A clinical close-up photograph of a skin lesion. A male subject age 70:
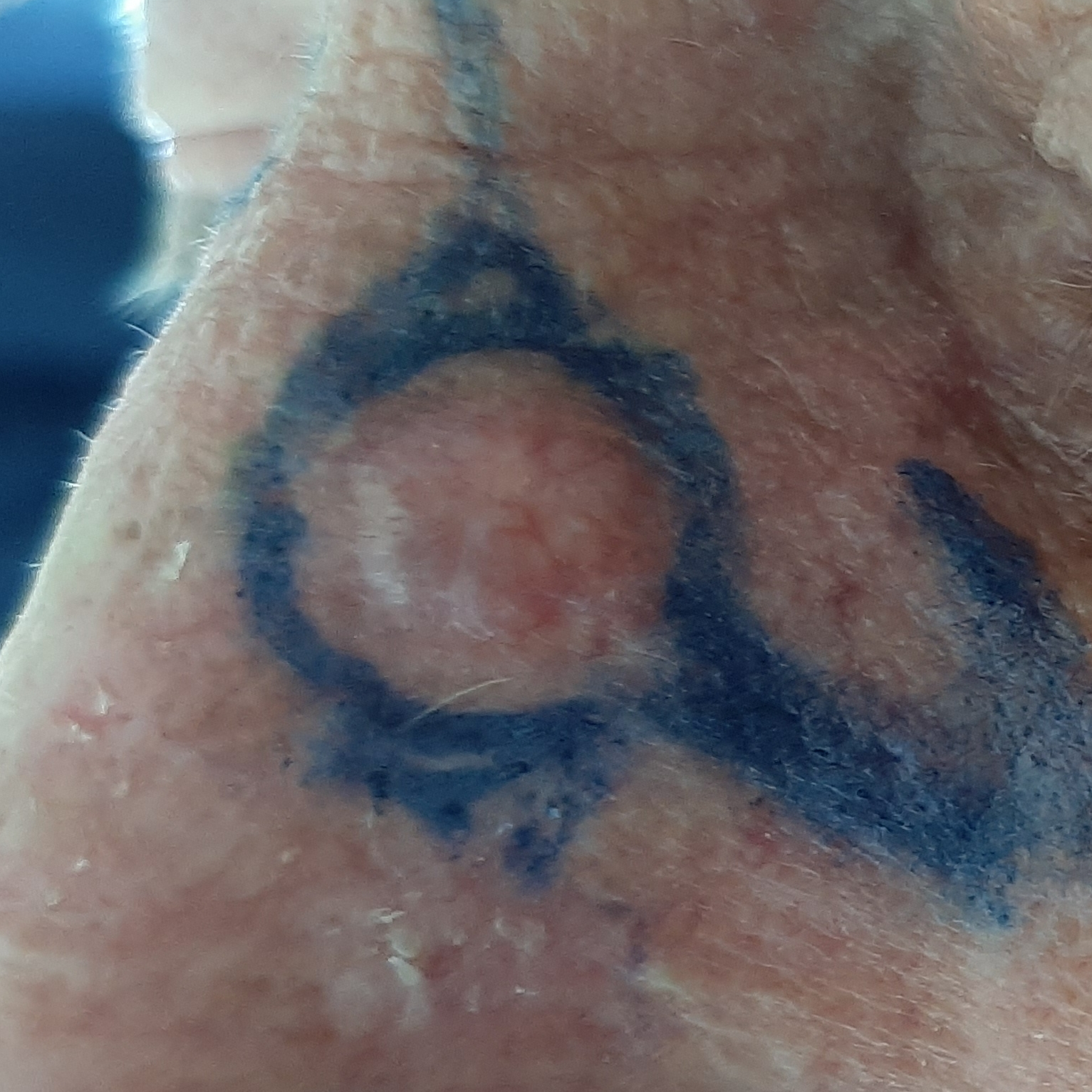{"symptoms": {"present": ["itching", "elevation"], "absent": ["bleeding"]}, "diagnosis": {"name": "basal cell carcinoma", "code": "BCC", "malignancy": "malignant", "confirmation": "histopathology"}}